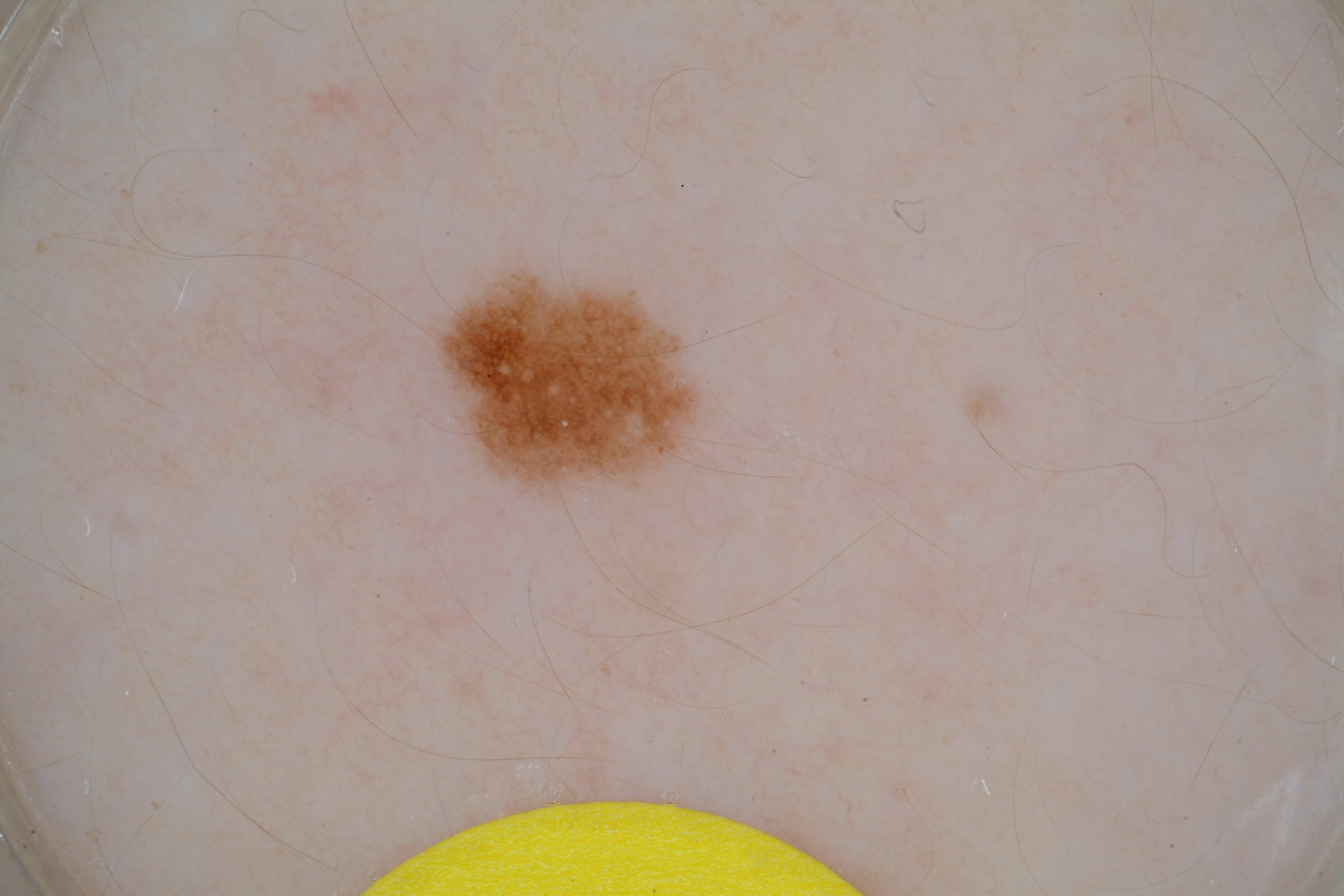- image type — dermoscopic image
- dermoscopic findings — milia-like cysts and pigment network; absent: streaks and negative network
- lesion location — (433, 256, 717, 503)
- diagnostic label — a melanocytic nevus, a benign lesion